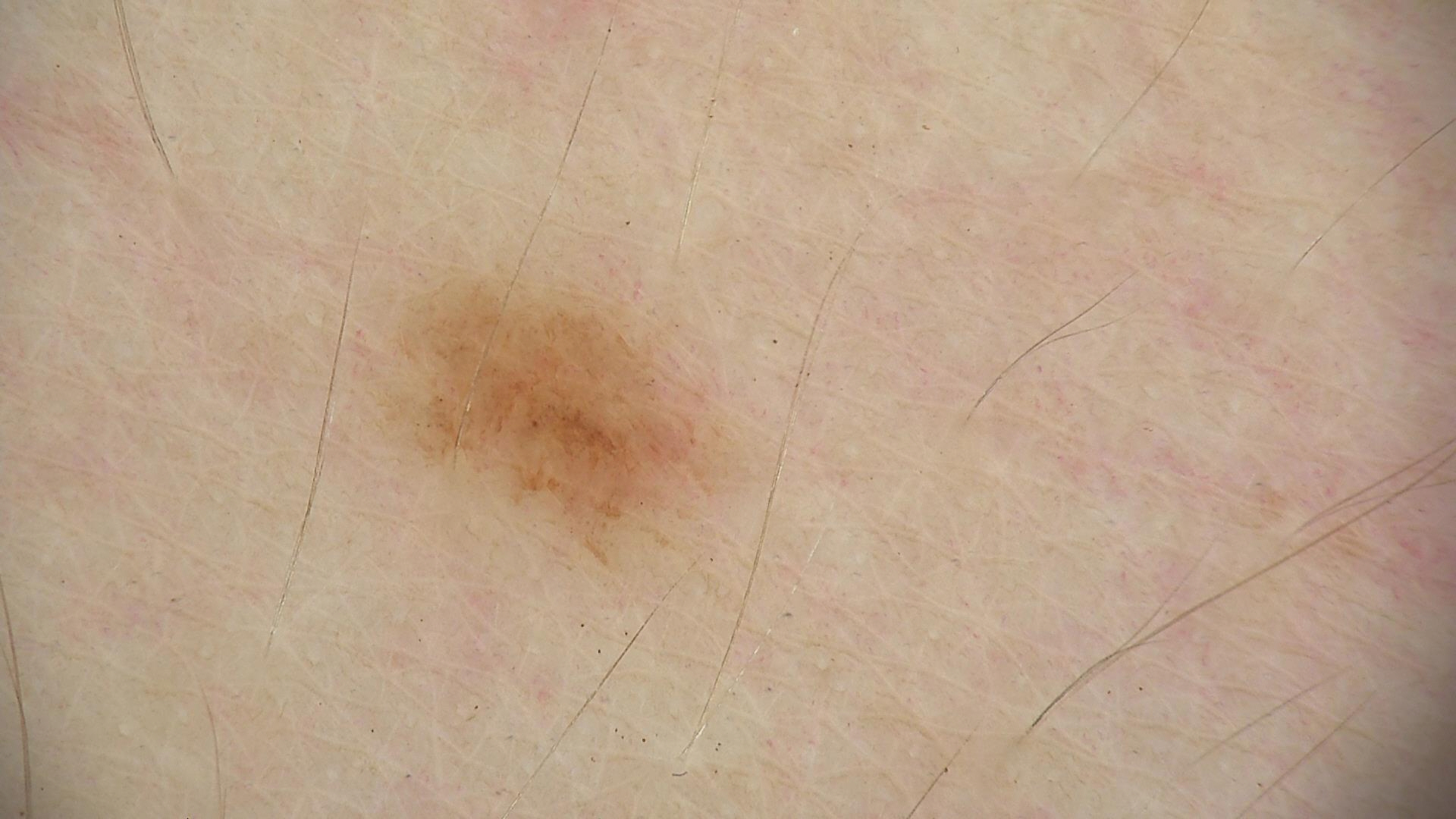image type: dermoscopy
diagnosis: dysplastic junctional nevus (expert consensus)